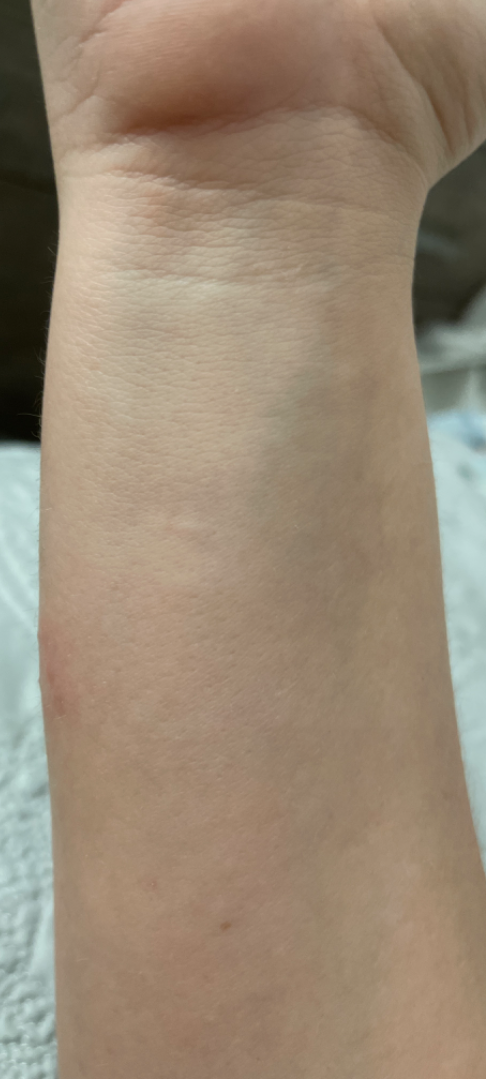• assessment — no discernible pathology